A dermoscopic close-up of a skin lesion:
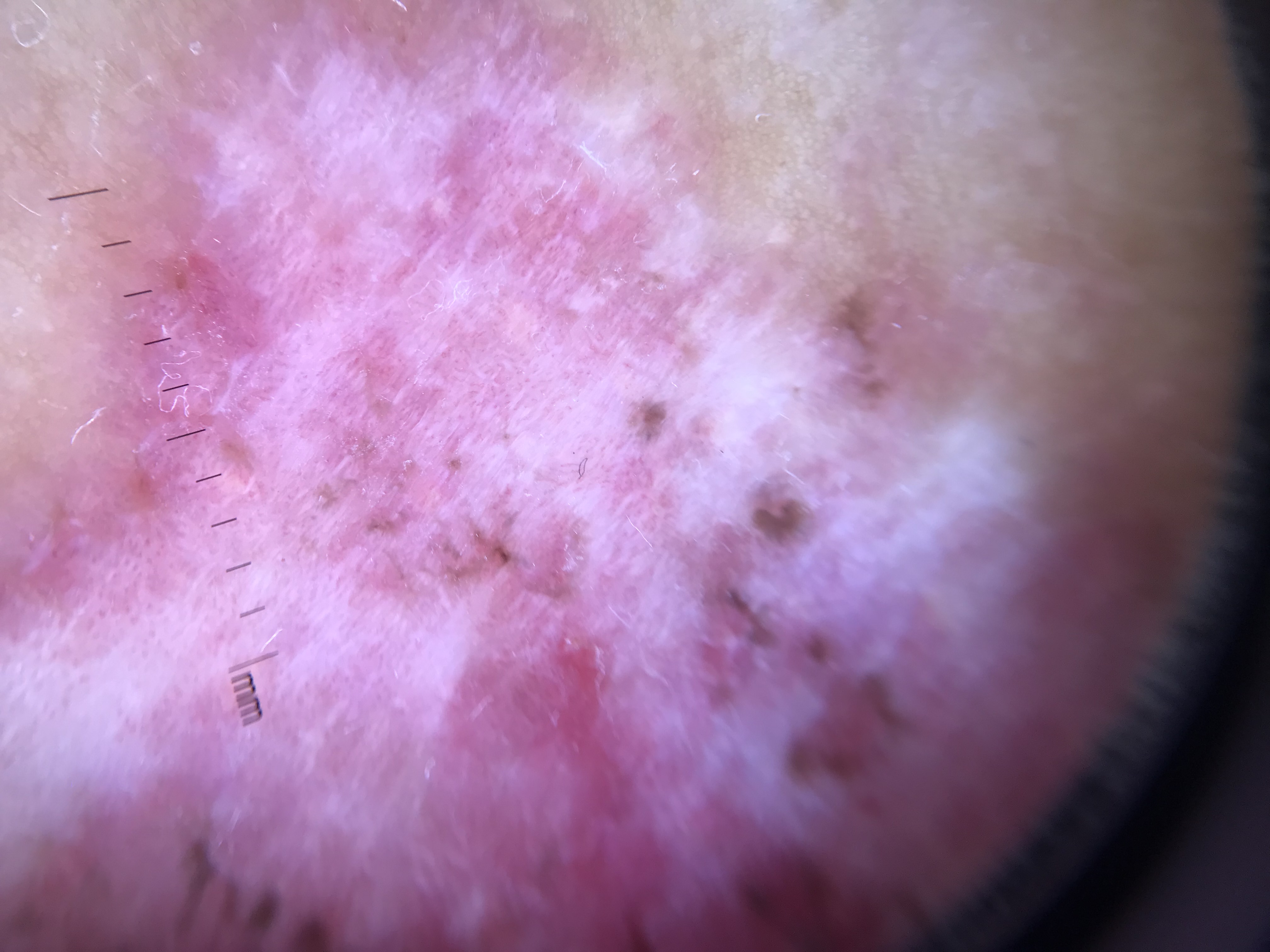lesion type = keratinocytic
diagnosis = basal cell carcinoma (biopsy-proven)